The patient considered this a rash. Present for three to twelve months. Reported lesion symptoms include burning, itching and bothersome appearance. Texture is reported as raised or bumpy. This image was taken at a distance: 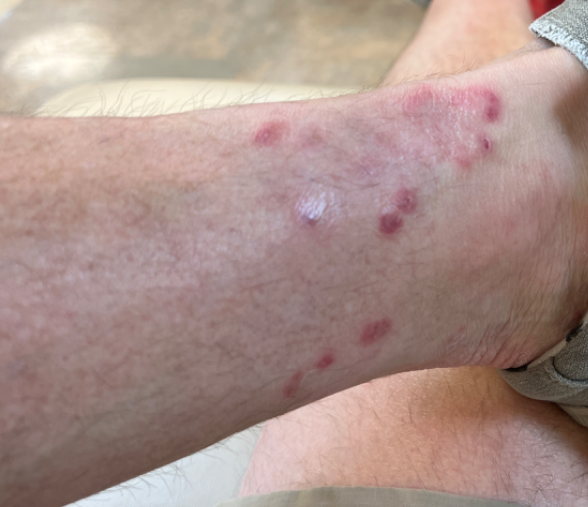{
  "differential": {
    "leading": [
      "Tinea"
    ],
    "considered": [
      "Granuloma annulare",
      "Eczema"
    ]
  }
}